Self-categorized by the patient as a rash · the patient reports enlargement and itching · female contributor, age 50–59 · the affected area is the arm · this is a close-up image · present for less than one week · skin tone: Fitzpatrick III; non-clinician graders estimated 3 on the MST — 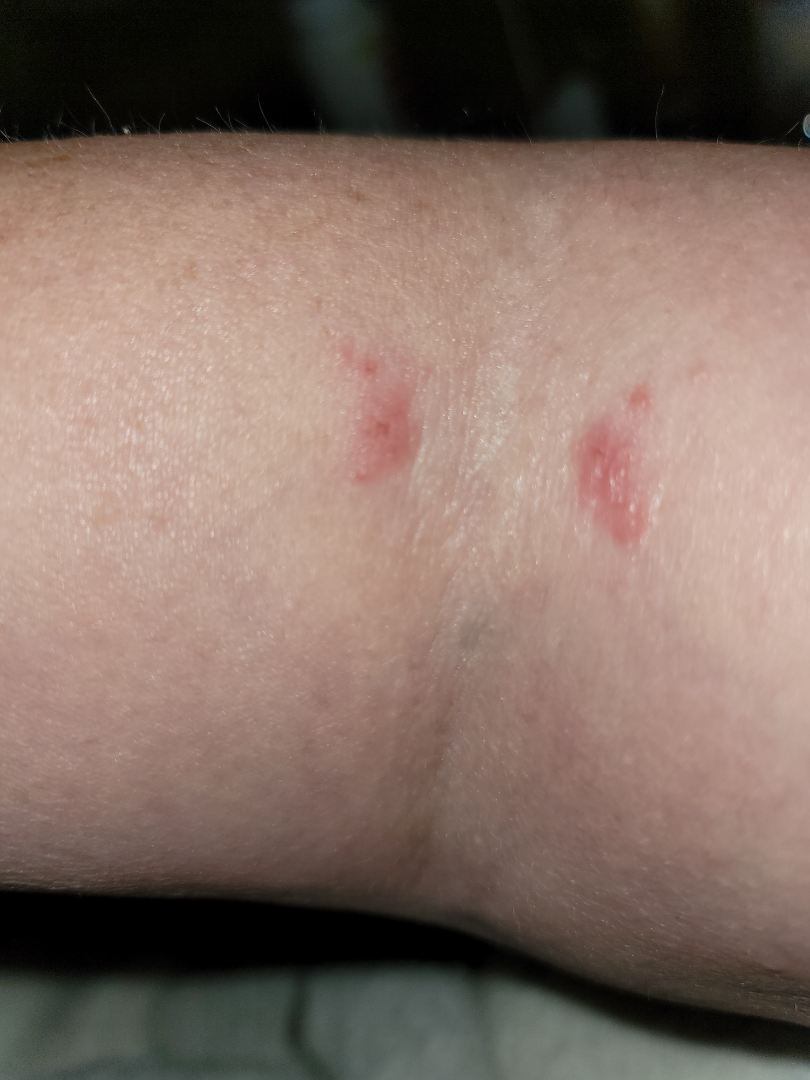Findings:
* differential · reviewed remotely by one dermatologist: the reviewer's impression was Eczema